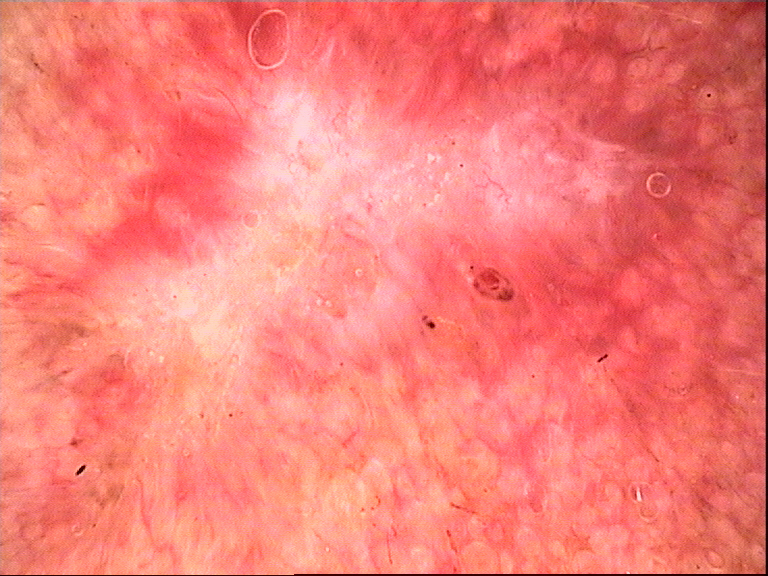Q: What is this lesion?
A: basal cell carcinoma (biopsy-proven)